Located on the leg; the contributor is female; the photo was captured at a distance:
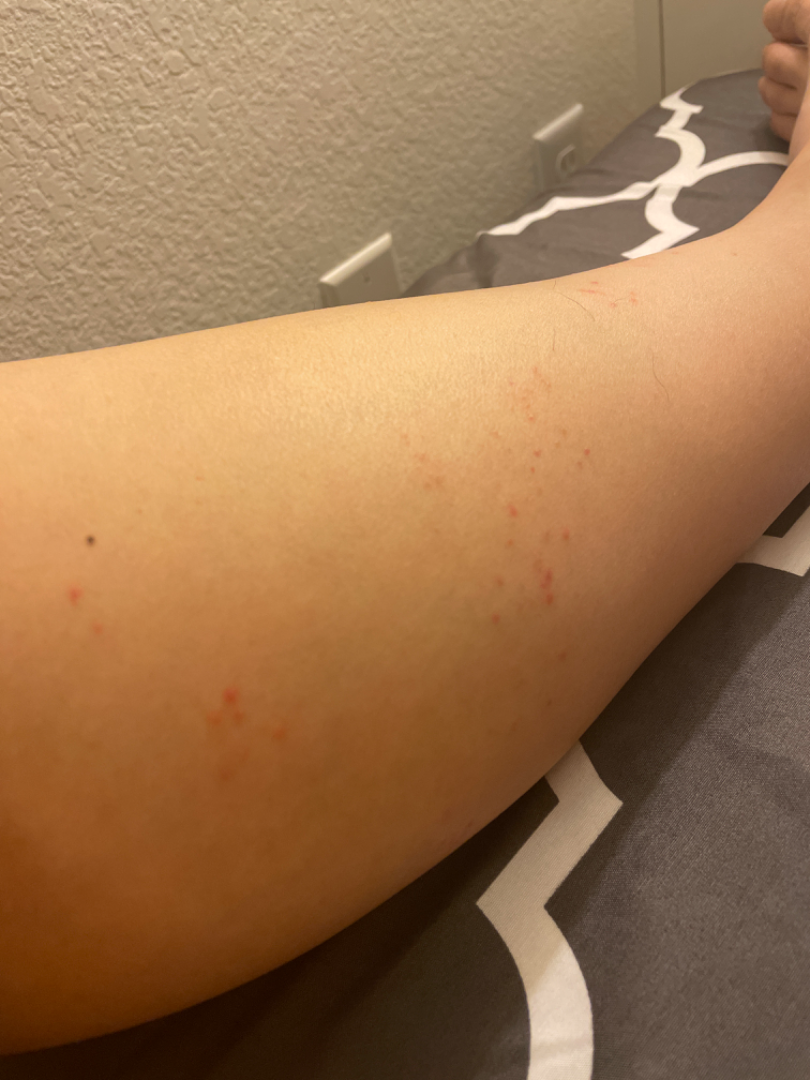Folliculitis (most likely); Insect Bite (considered); Allergic Contact Dermatitis (considered).